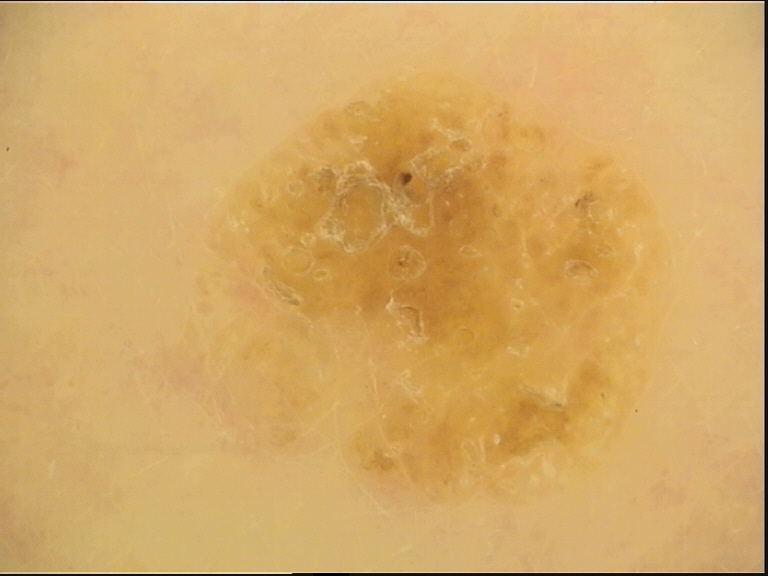Impression: Labeled as a seborrheic keratosis.